A skin lesion imaged with a dermatoscope: 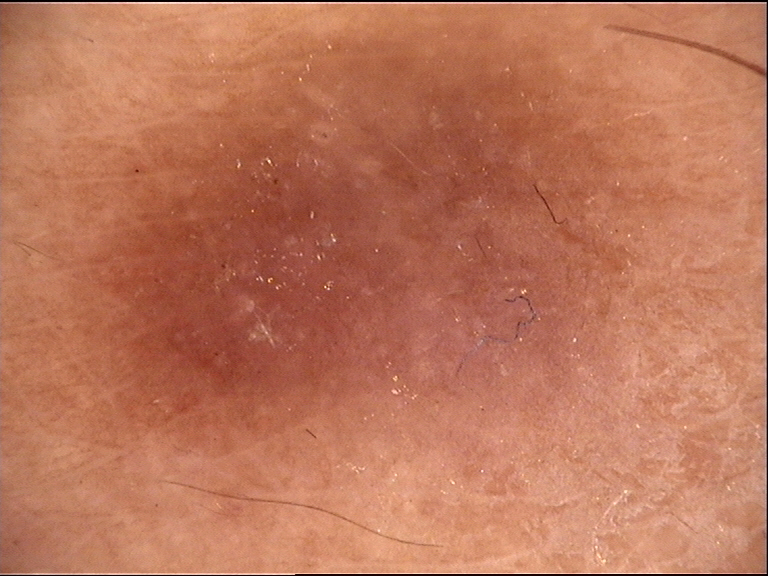Summary: The architecture is that of a fibro-histiocytic lesion. Impression: The diagnosis was a dermatofibroma.